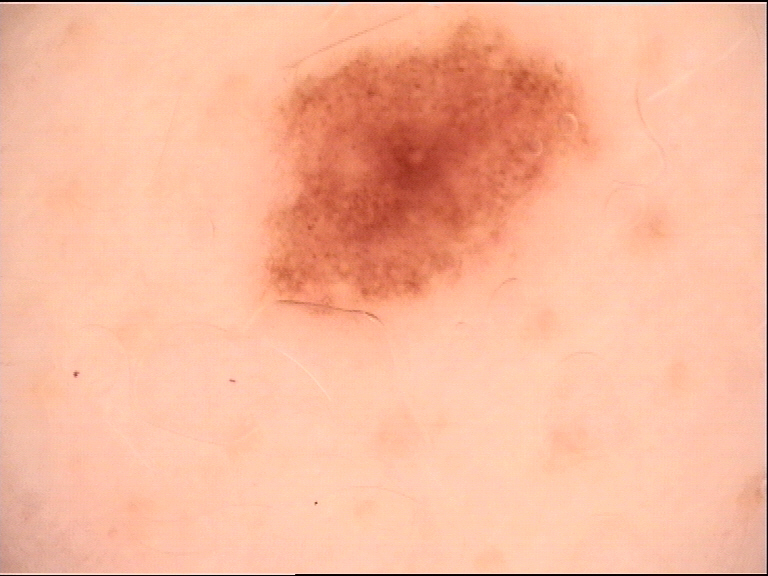class=dysplastic compound nevus (expert consensus)